The patient described the issue as acne; symptoms reported: bothersome appearance; present for about one day; located on the arm; the patient indicates the lesion is fluid-filled; no constitutional symptoms were reported; this image was taken at an angle: 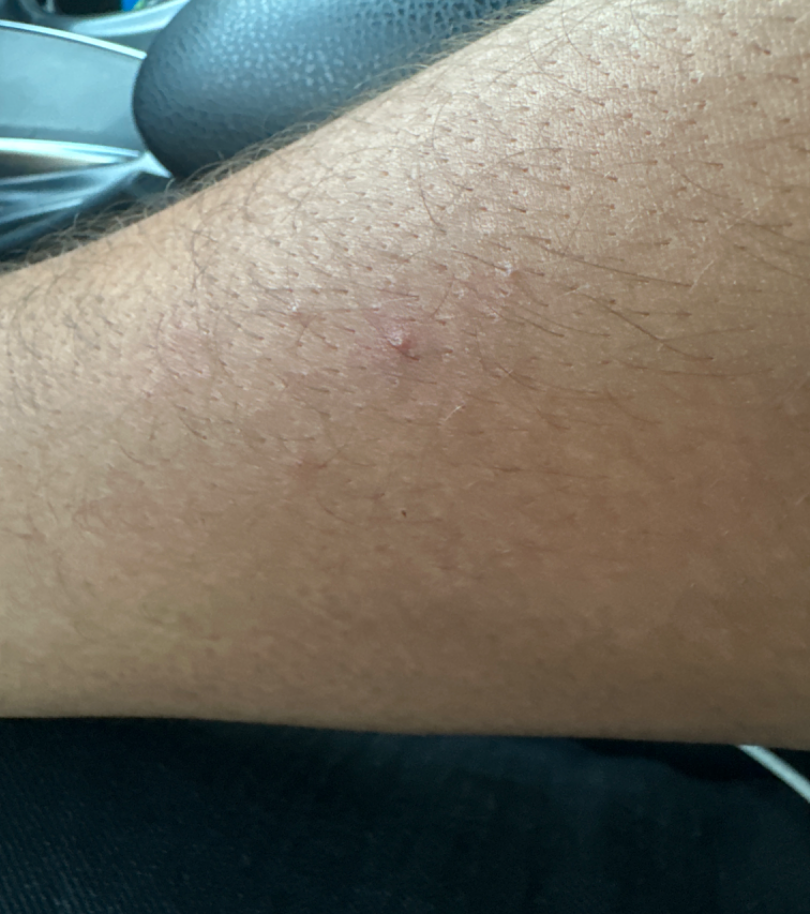On photographic review, the leading consideration is Eczema; also on the differential is Keratosis pilaris.